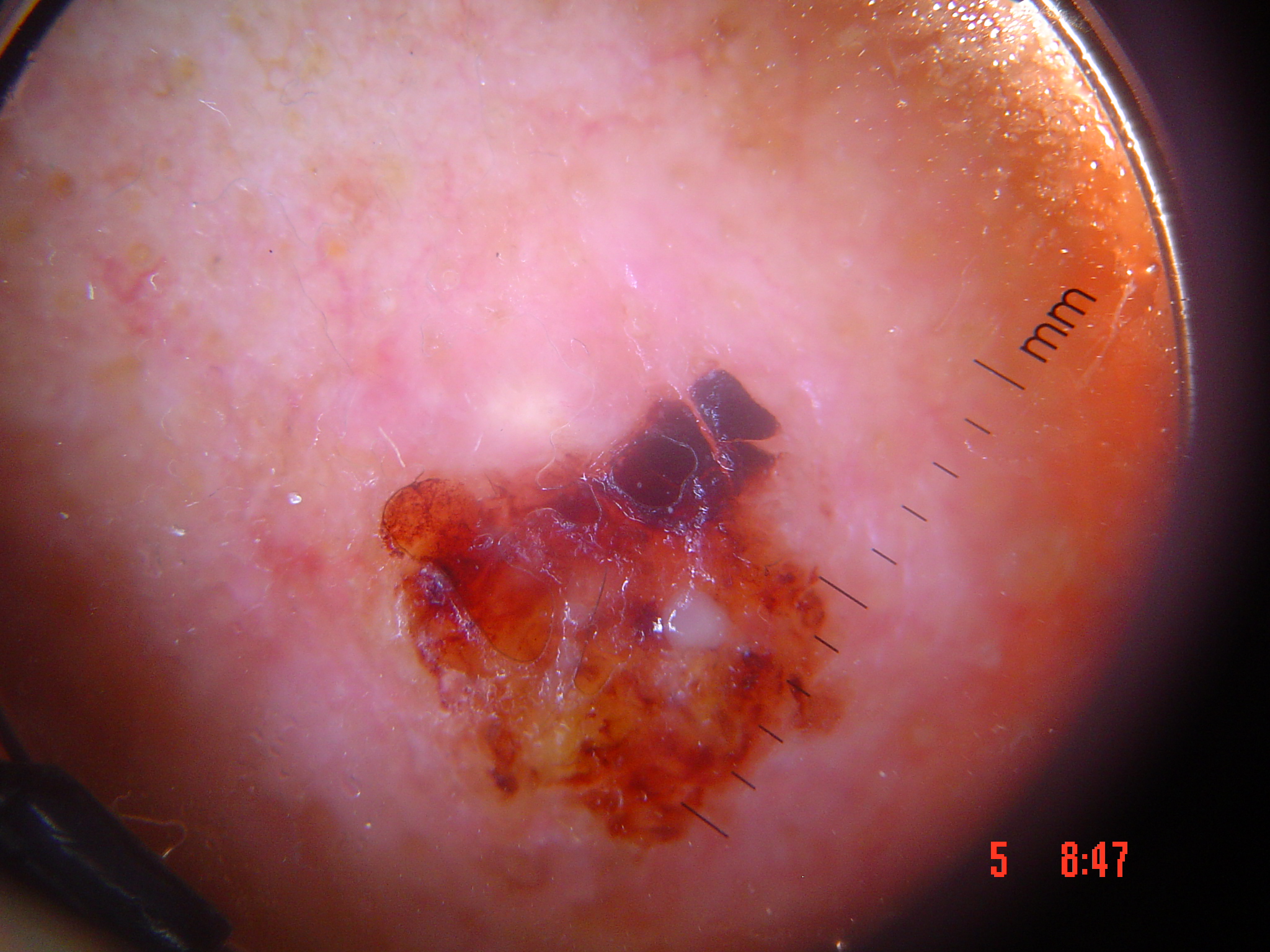image = dermatoscopy
classification = keratinocytic
class = squamous cell carcinoma (biopsy-proven)